An image taken at a distance:
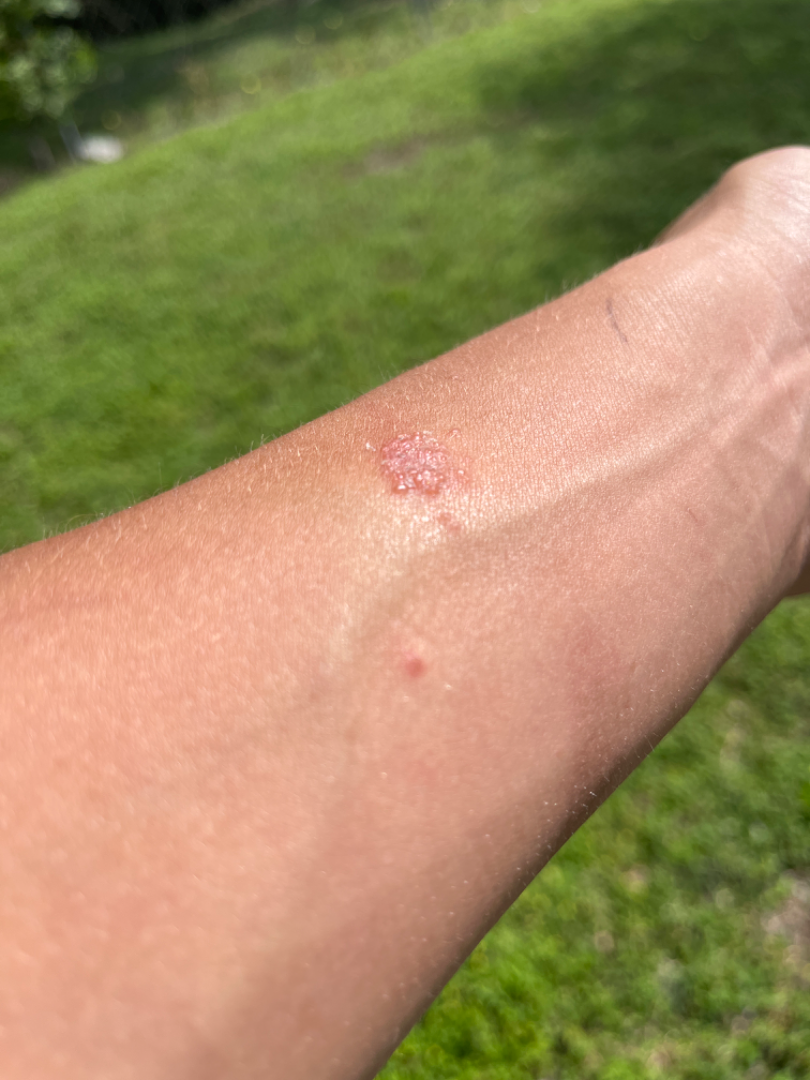The reviewing dermatologist was unable to assign a differential diagnosis from the image.